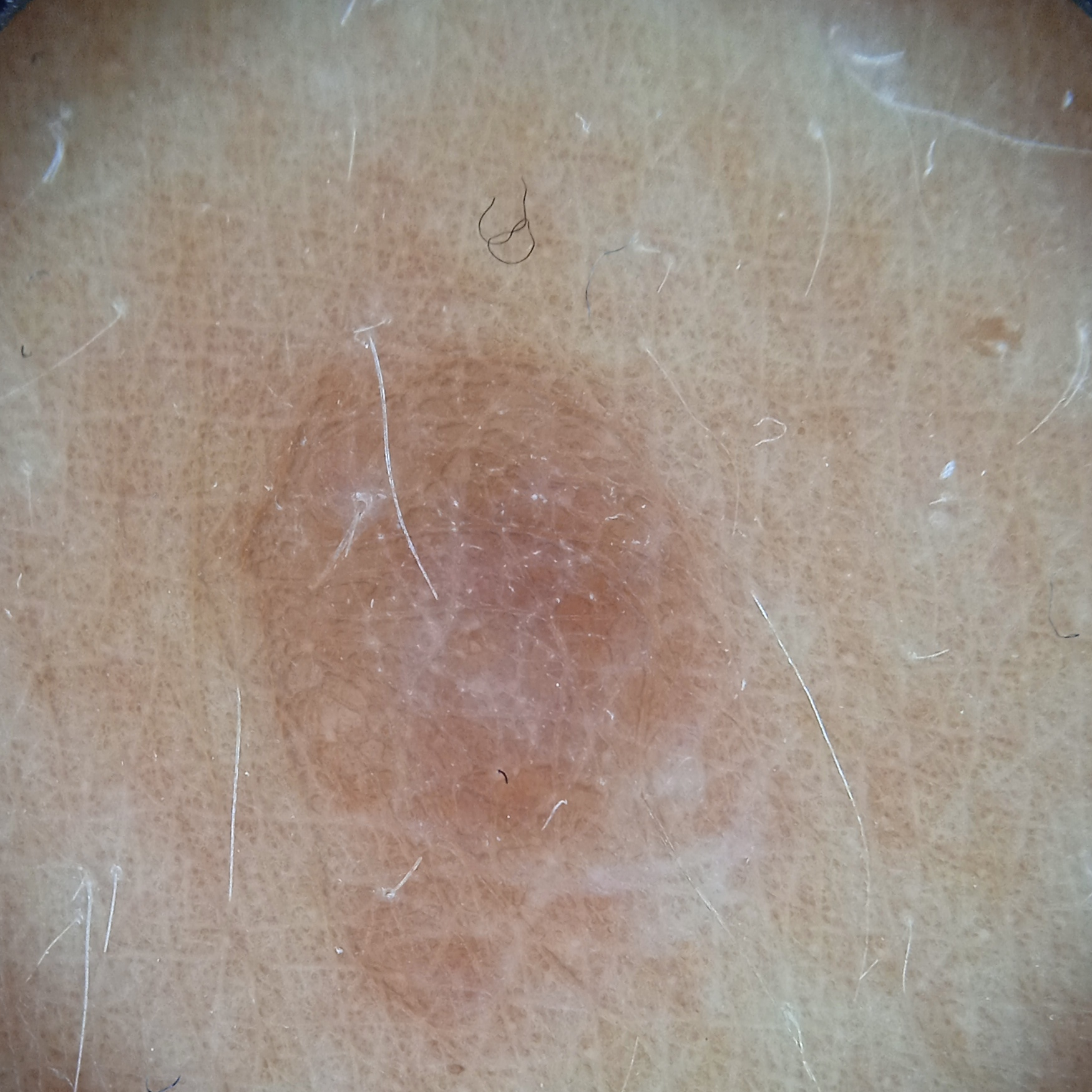The reviewing dermatologists could not reach a confident diagnosis. <case>
<referral>research study (no referral diagnosis)</referral>
<image>dermoscopy</image>
<patient>
<age>47</age>
<sex>female</sex>
</patient>
<lesion_location>an arm</lesion_location>
<lesion_size>
<diameter_mm>8.1</diameter_mm>
</lesion_size>
</case>